A clinical photograph showing a skin lesion. The patient says their skin reddens with sun exposure. A male patient aged 60. The referring clinician suspected basal cell carcinoma — 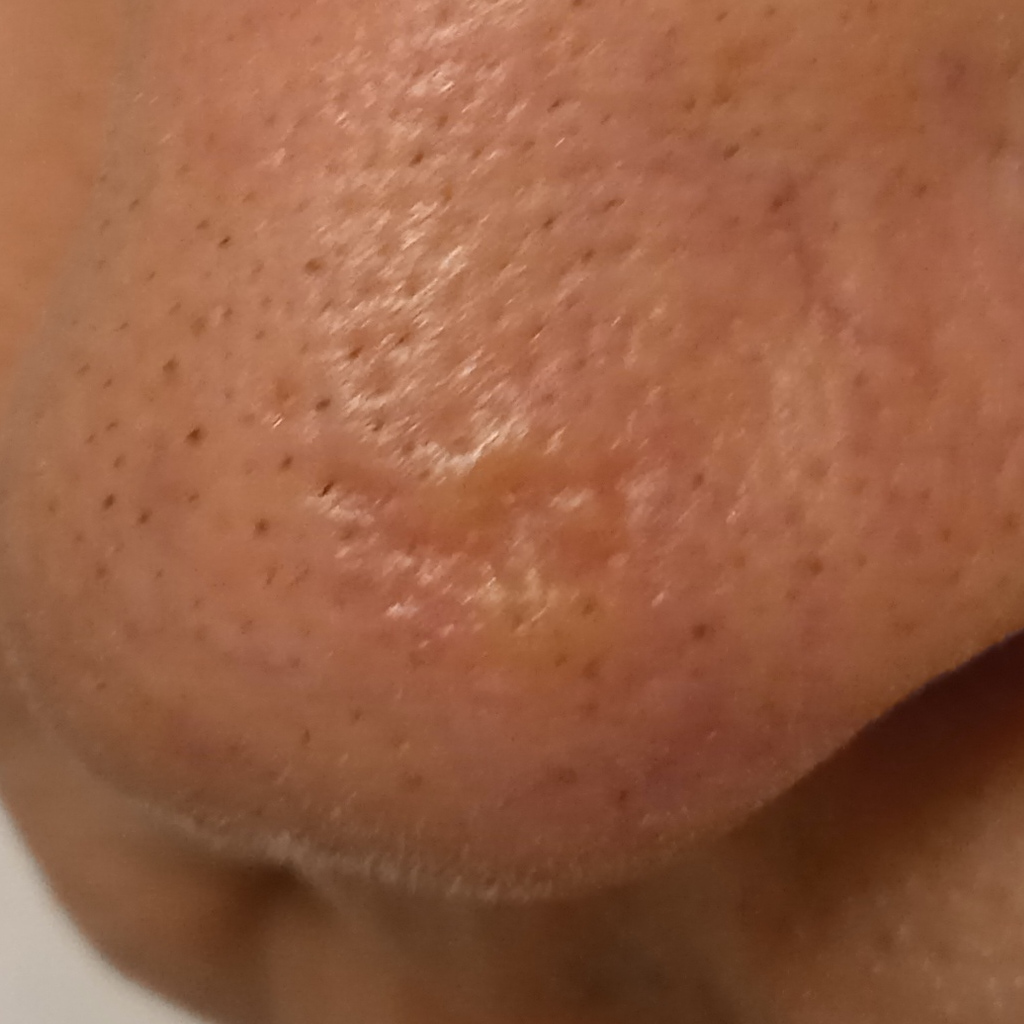Clinical context:
The lesion is on the face. Measuring roughly 8.5 mm.
Diagnosis:
Histopathology confirmed a basal cell carcinoma, following excision, with a measured tumor thickness of 1.7 mm.